A skin lesion imaged with a dermatoscope: 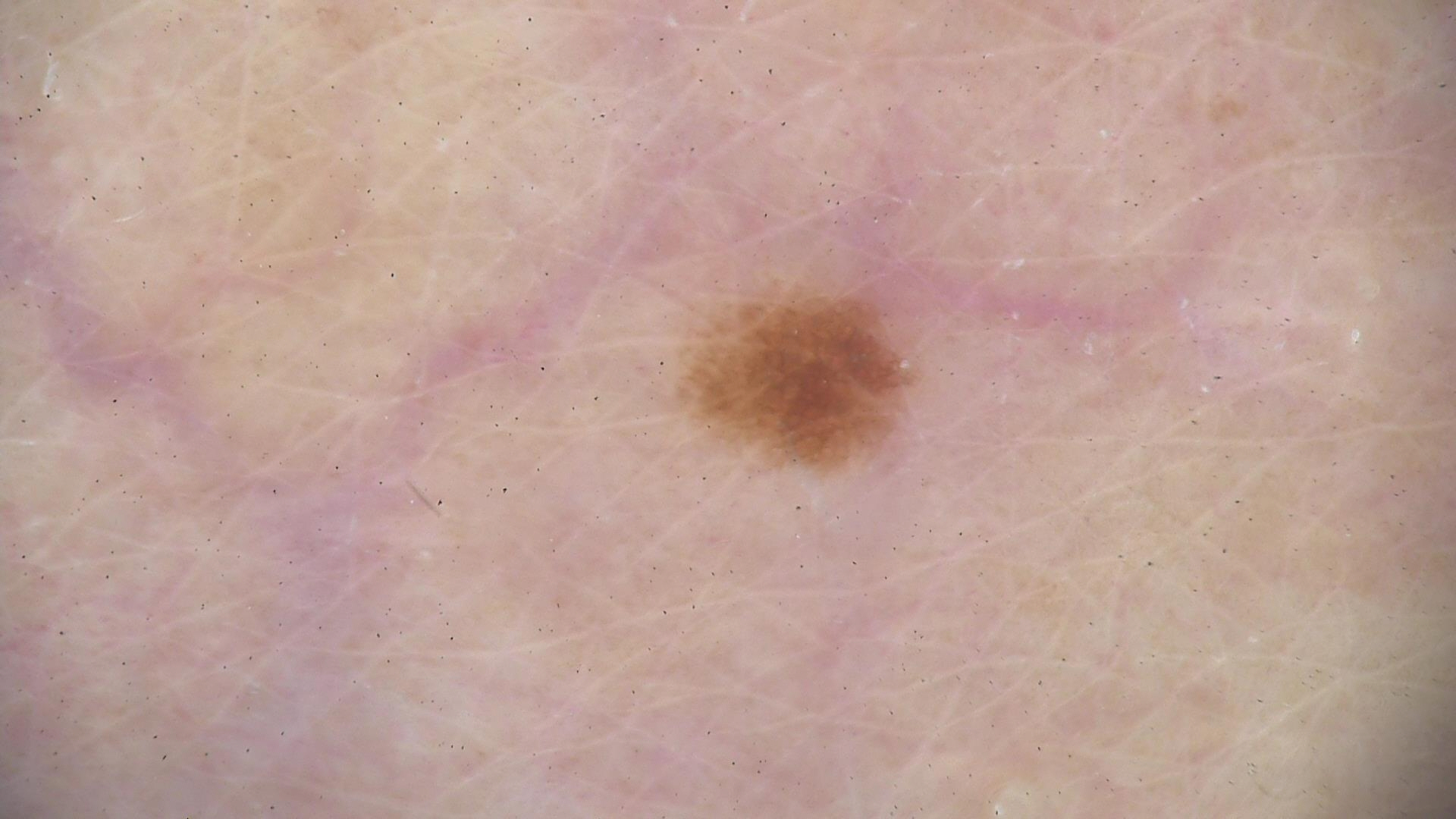The architecture is that of a banal lesion. The diagnostic label was a junctional nevus.